Contact-polarized dermoscopy of a skin lesion: 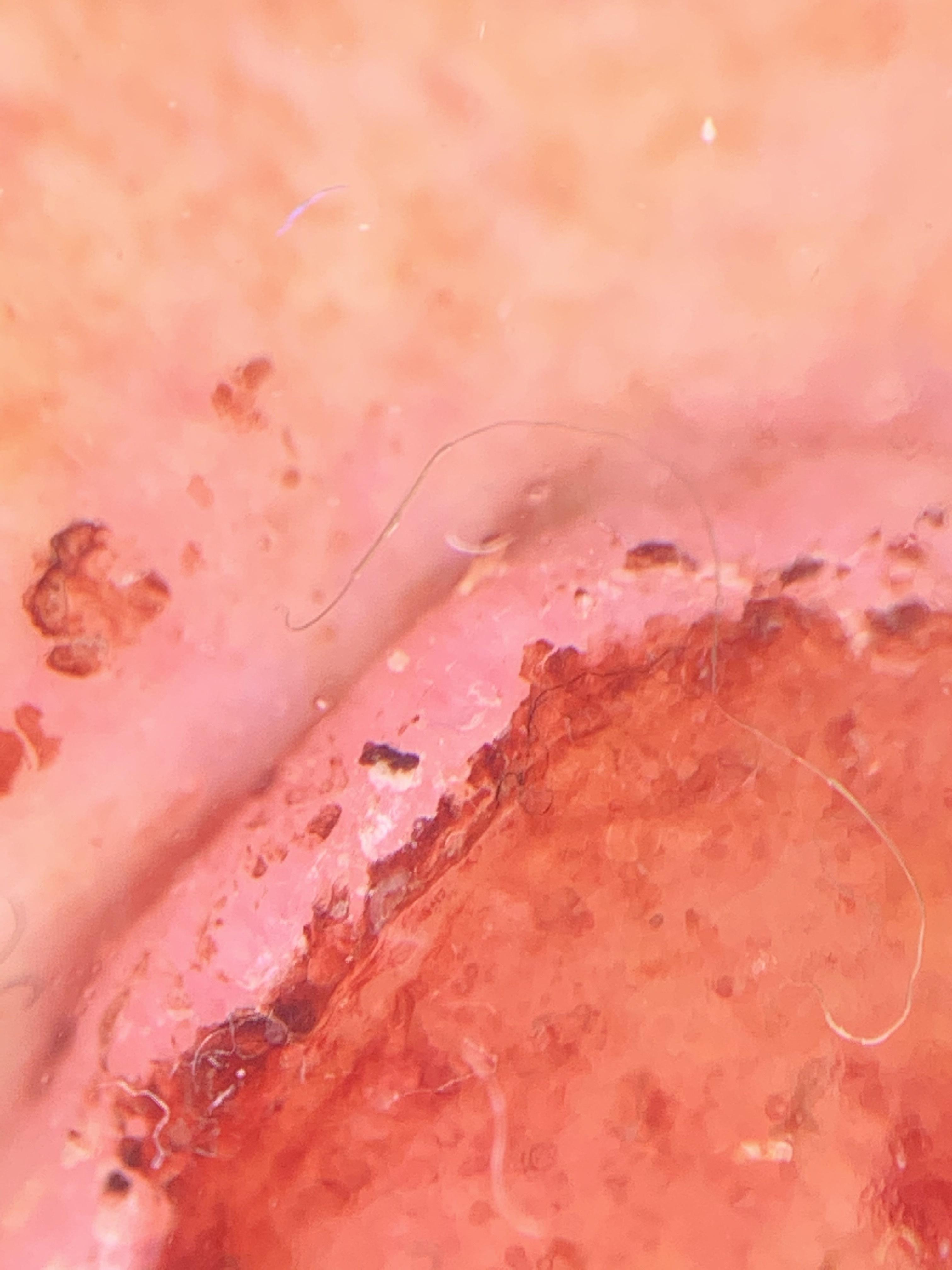Q: What is the anatomic site?
A: the head or neck
Q: What is this lesion?
A: Squamous cell carcinoma (biopsy-proven)